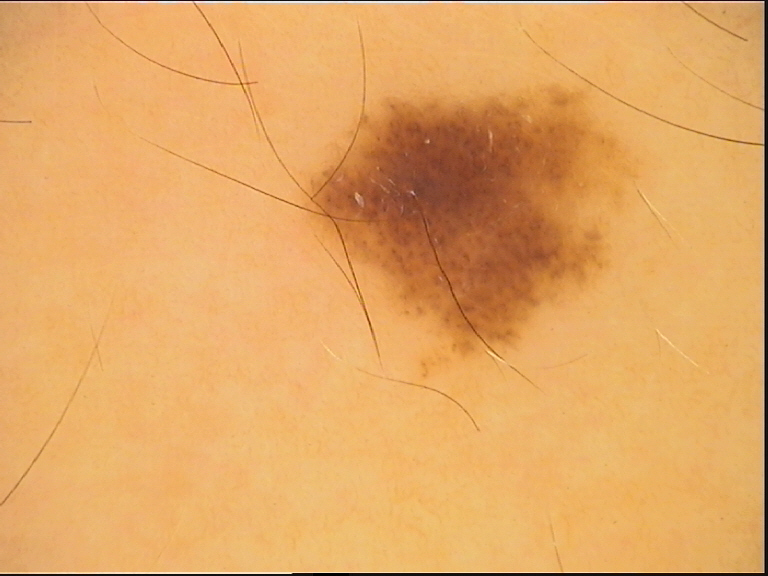Findings:
– class: dysplastic junctional nevus (expert consensus)